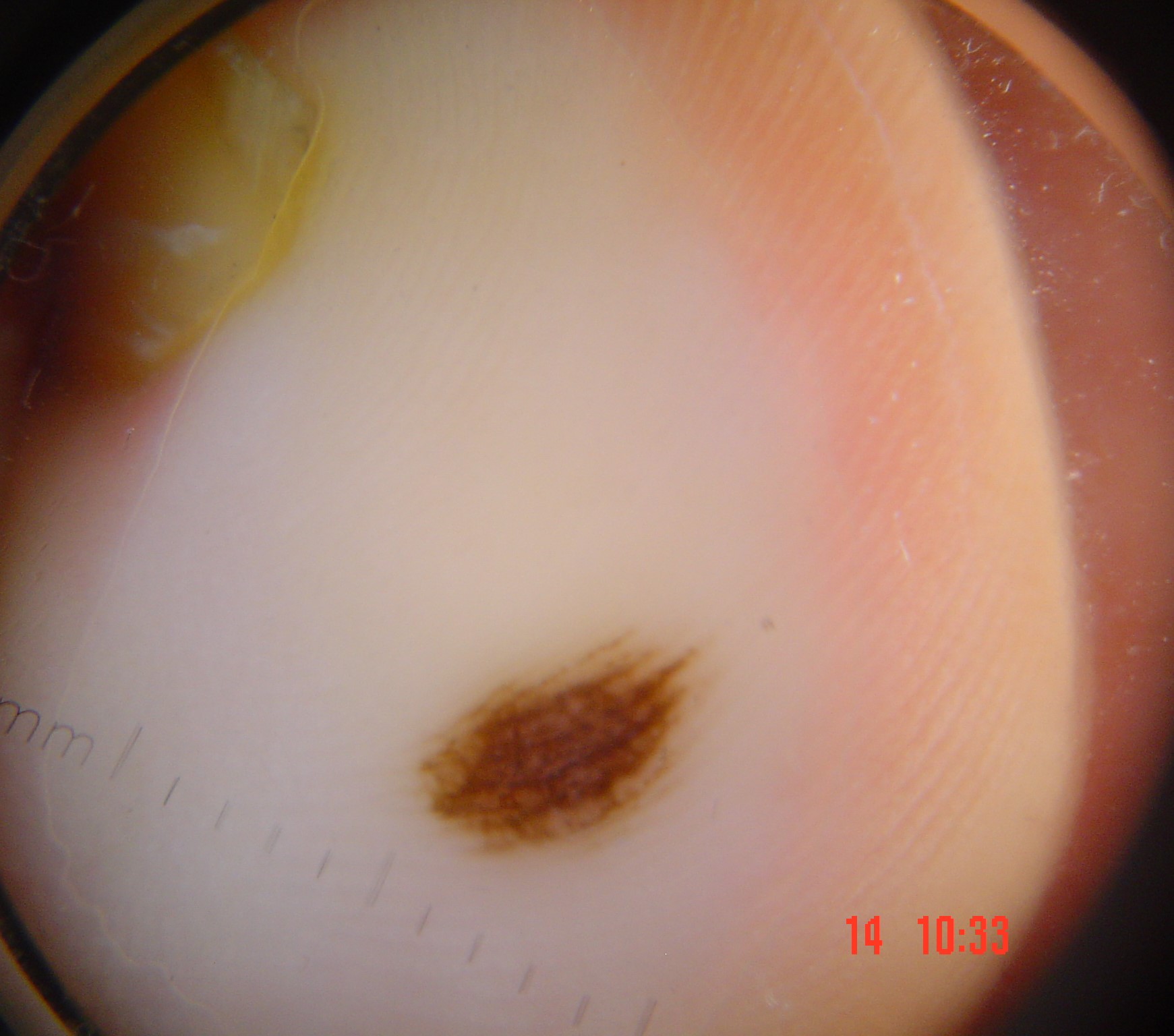Labeled as an acral dysplastic junctional nevus.